The photograph was taken at an angle. The patient is a female aged 18–29. The leg is involved.
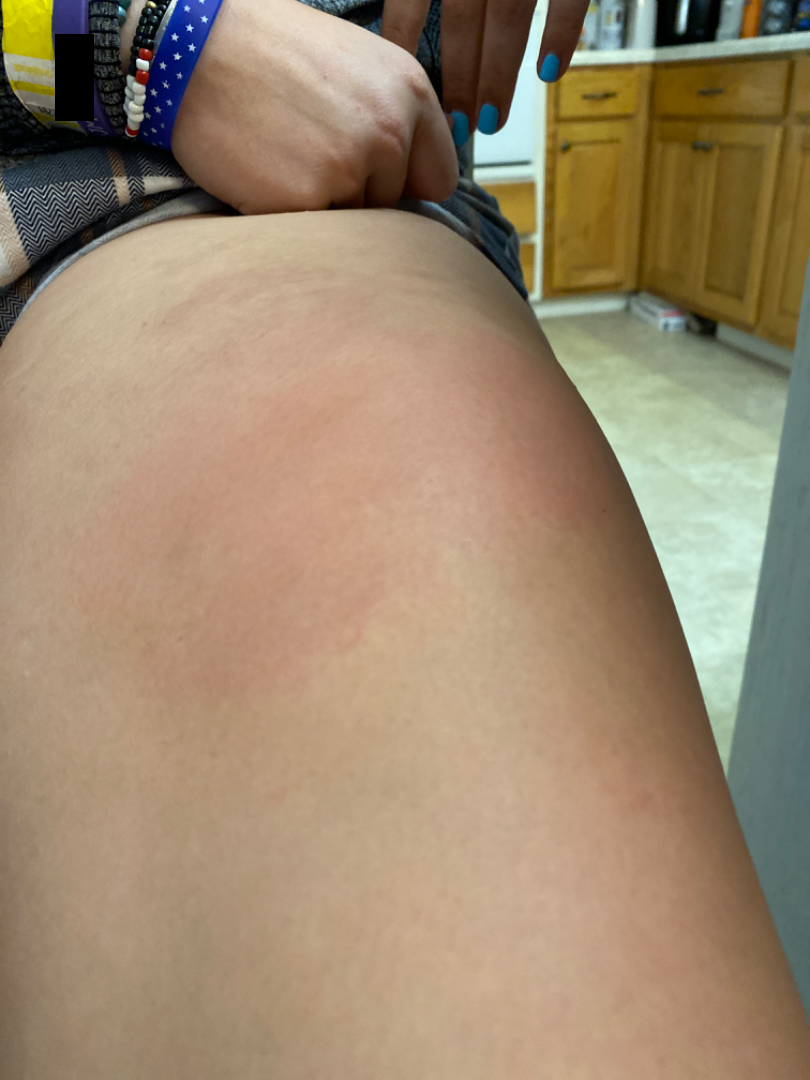The patient considered this a rash.
Reported lesion symptoms include enlargement and itching.
Present for one to four weeks.
The contributor reports the lesion is raised or bumpy.
On remote review of the image: most consistent with Hypersensitivity; with consideration of Urticaria.